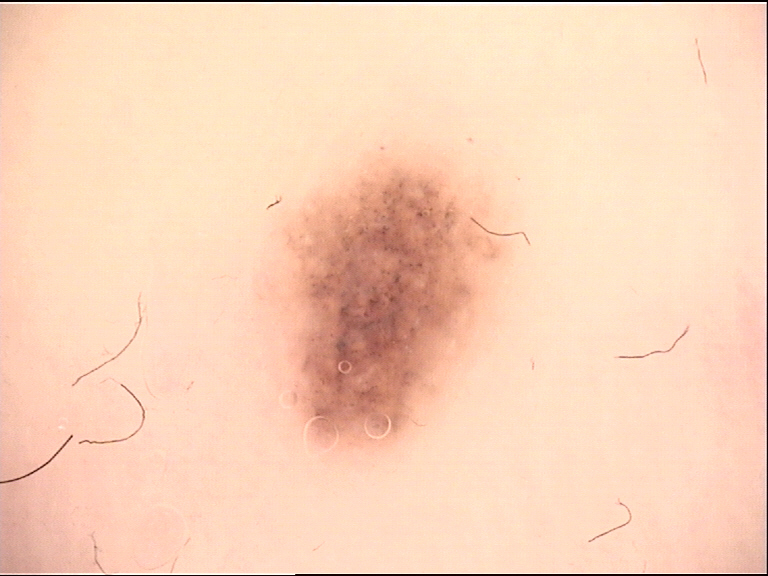Impression: The diagnosis was an acral dysplastic junctional nevus.